The patient describes having a moderate number of moles; a macroscopic clinical photograph of a skin lesion; a female subject 55 years of age; imaged for a research study, with no referral diagnosis recorded; by self-report, immunosuppression, a prior organ transplant, no family history of skin cancer, and no sunbed use; the patient says their skin reddens painfully with sun exposure.
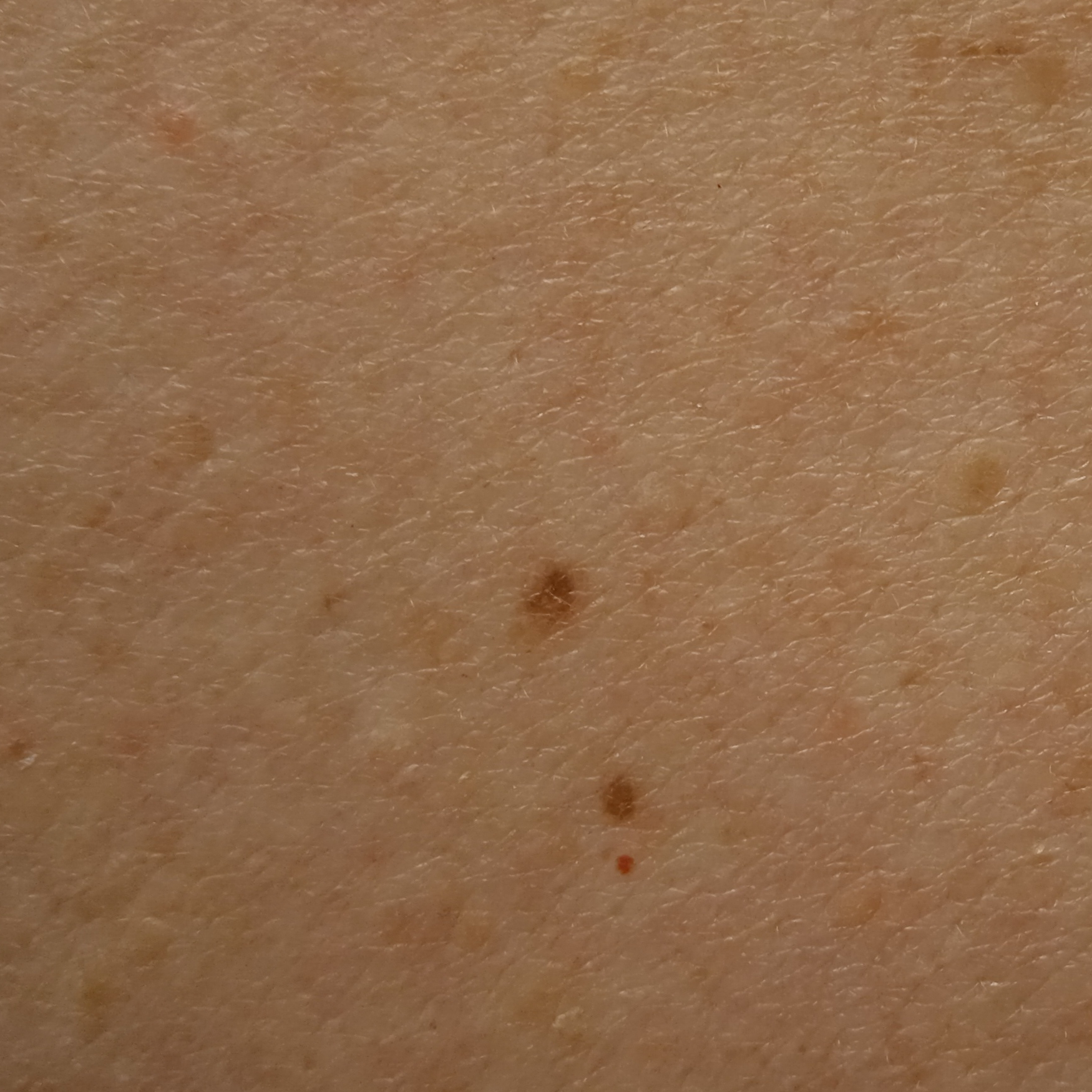{
  "lesion_location": "the back",
  "lesion_size": {
    "diameter_mm": 2.5
  },
  "diagnosis": {
    "name": "melanocytic nevus",
    "malignancy": "benign"
  }
}